A dermoscopy image of a single skin lesion.
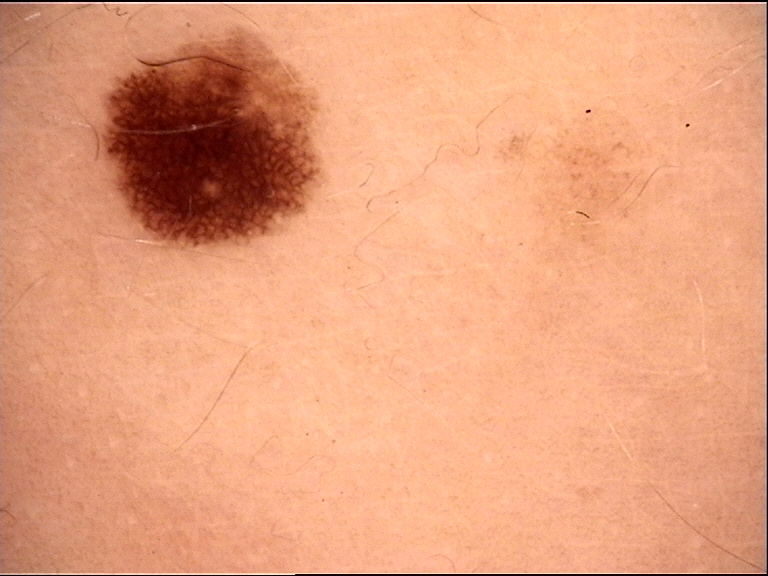Classified as a benign lesion — a dysplastic junctional nevus.